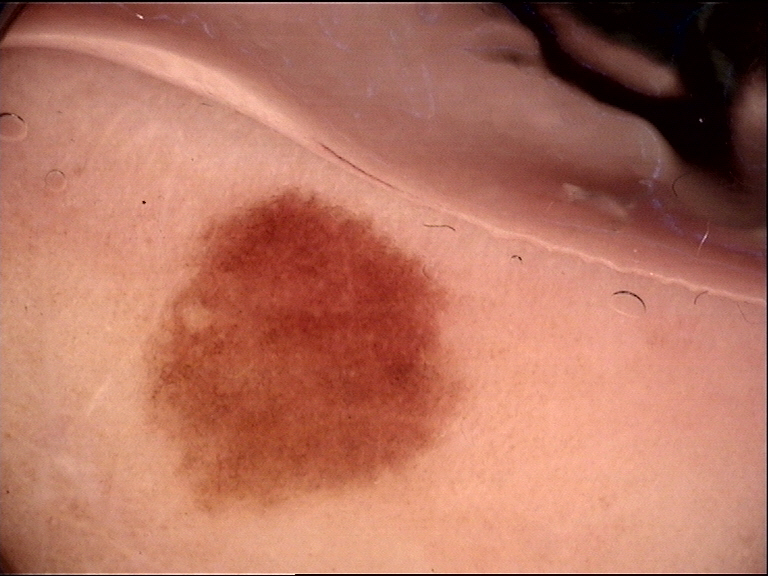assessment: dysplastic junctional nevus (expert consensus).